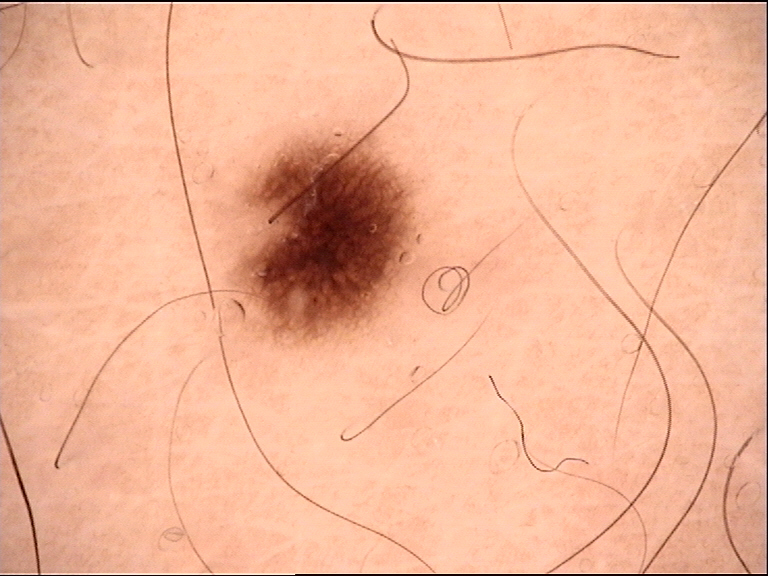<lesion>
  <image>dermoscopy</image>
  <lesion_type>
    <main_class>banal</main_class>
    <pattern>junctional</pattern>
  </lesion_type>
  <diagnosis>
    <name>junctional nevus</name>
    <code>jb</code>
    <malignancy>benign</malignancy>
    <super_class>melanocytic</super_class>
    <confirmation>expert consensus</confirmation>
  </diagnosis>
</lesion>